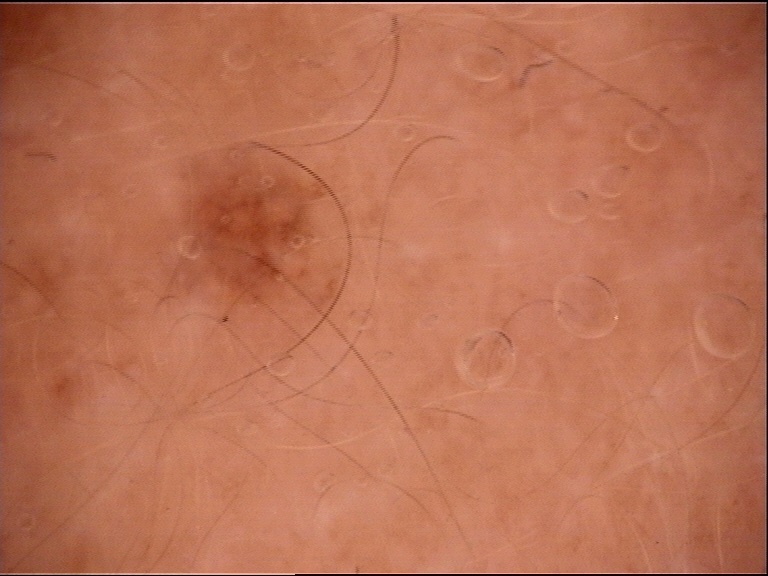Findings: A skin lesion imaged with a dermatoscope. Impression: Consistent with a banal lesion — a dermal nevus.